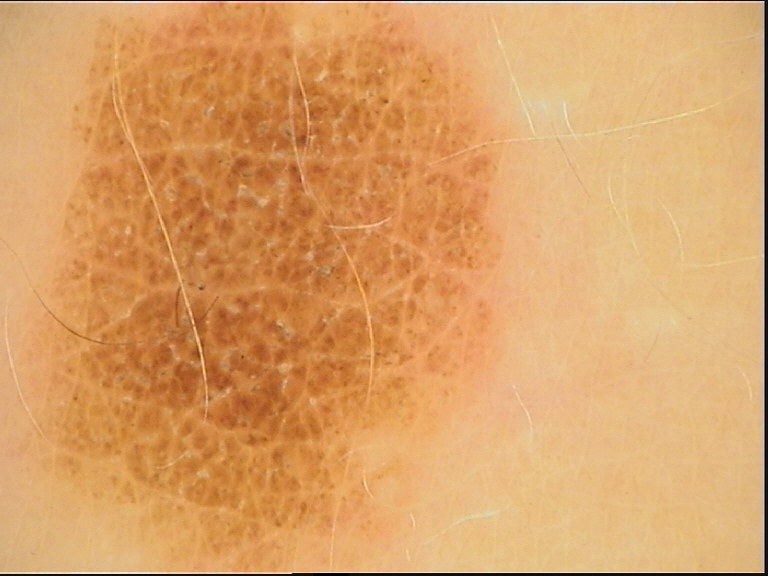Dermoscopy of a skin lesion.
Classified as a dysplastic compound nevus.